A subject in their mid-70s; a clinical close-up photograph of a skin lesion:
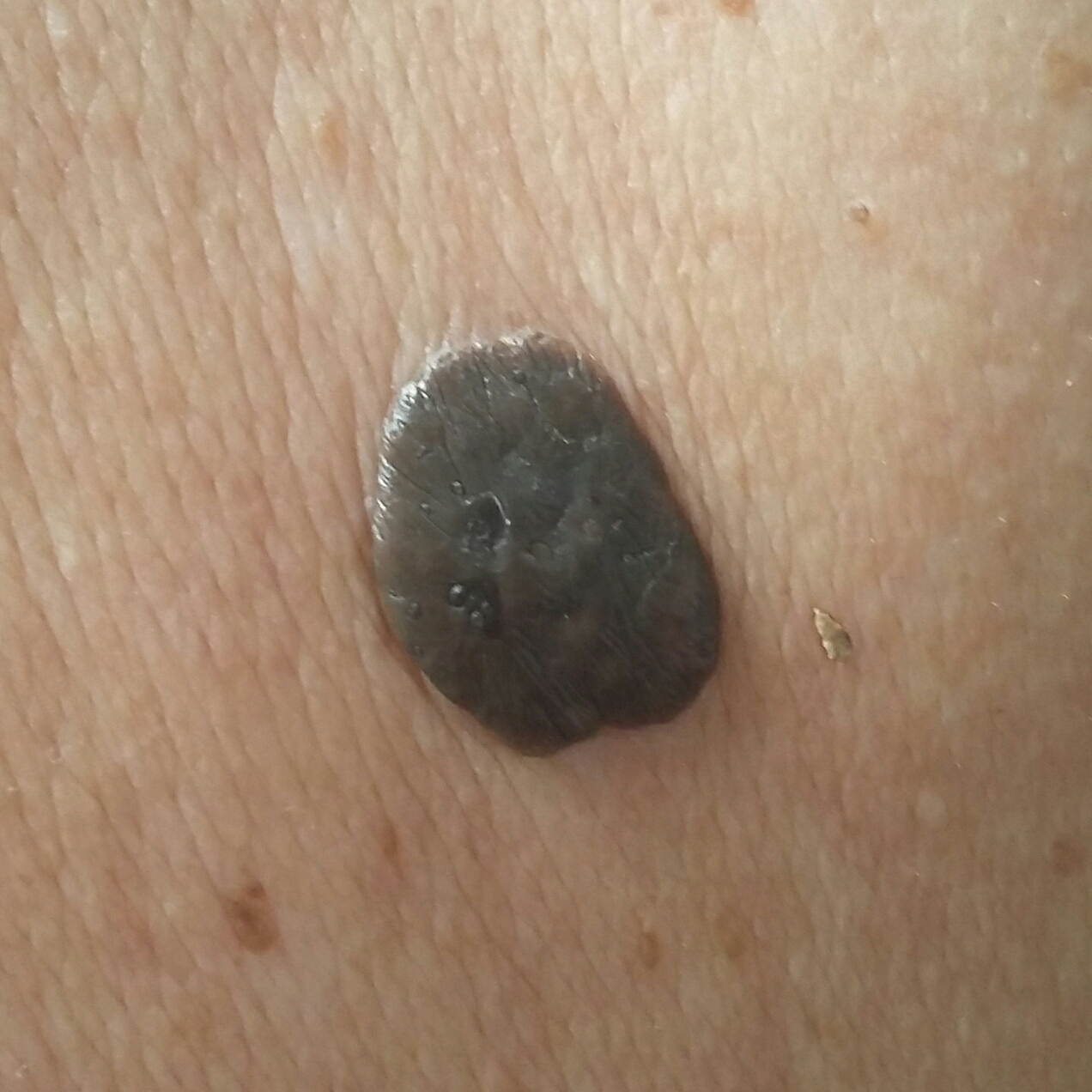body site=the back | reported symptoms=elevation | assessment=seborrheic keratosis (clinical consensus).